The lesion involves the arm · close-up view: 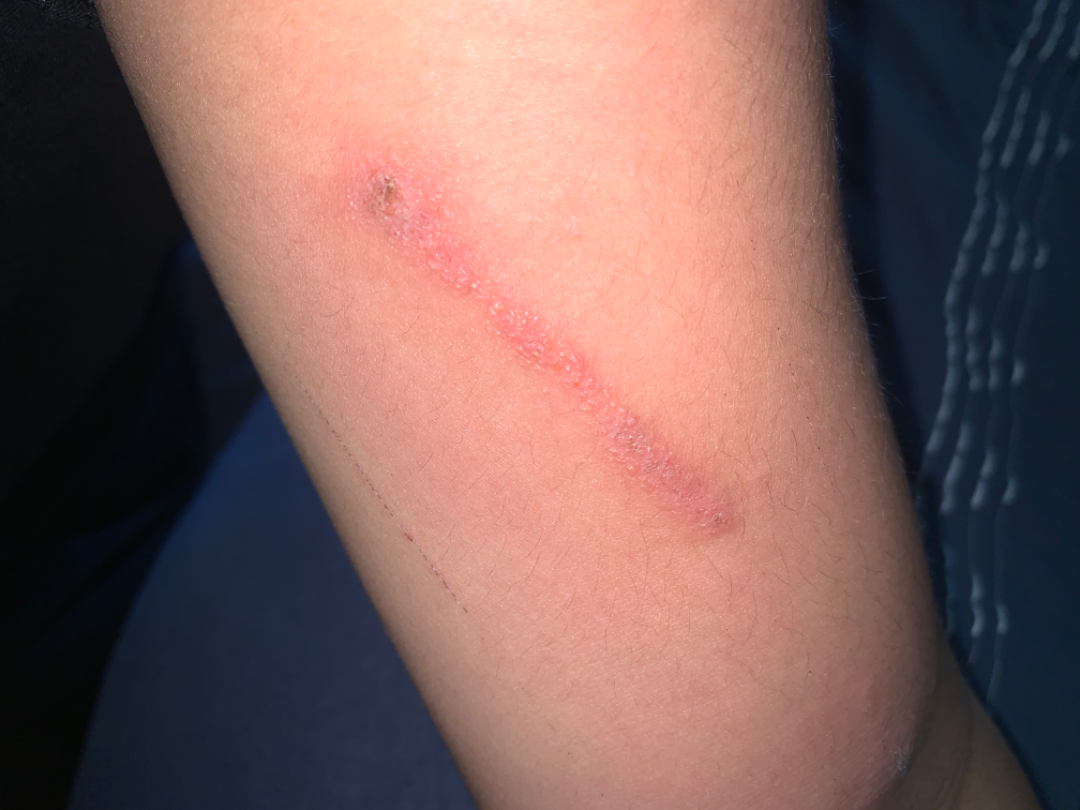The reviewing dermatologist's impression was: most likely wound/abrasion; also consider Allergic Contact Dermatitis; a remote consideration is Skin and soft tissue atypical mycobacterial infection.